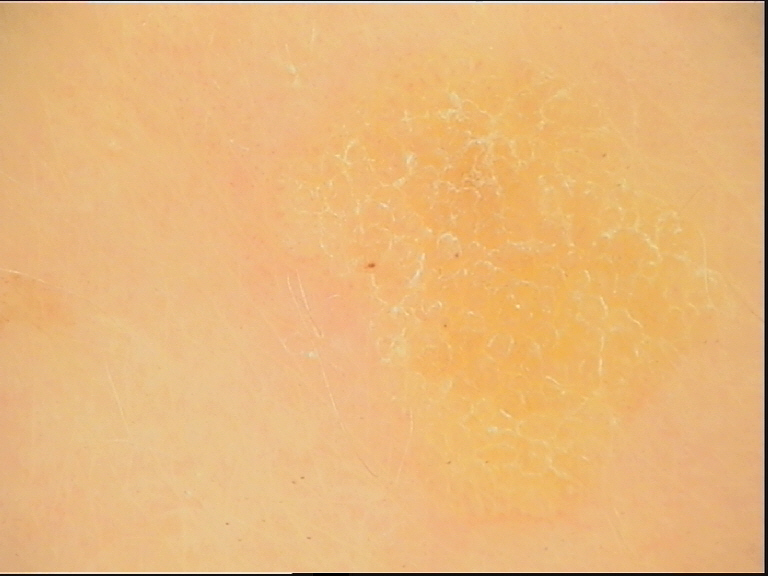Q: What kind of image is this?
A: dermoscopy
Q: What is this lesion?
A: seborrheic keratosis (expert consensus)